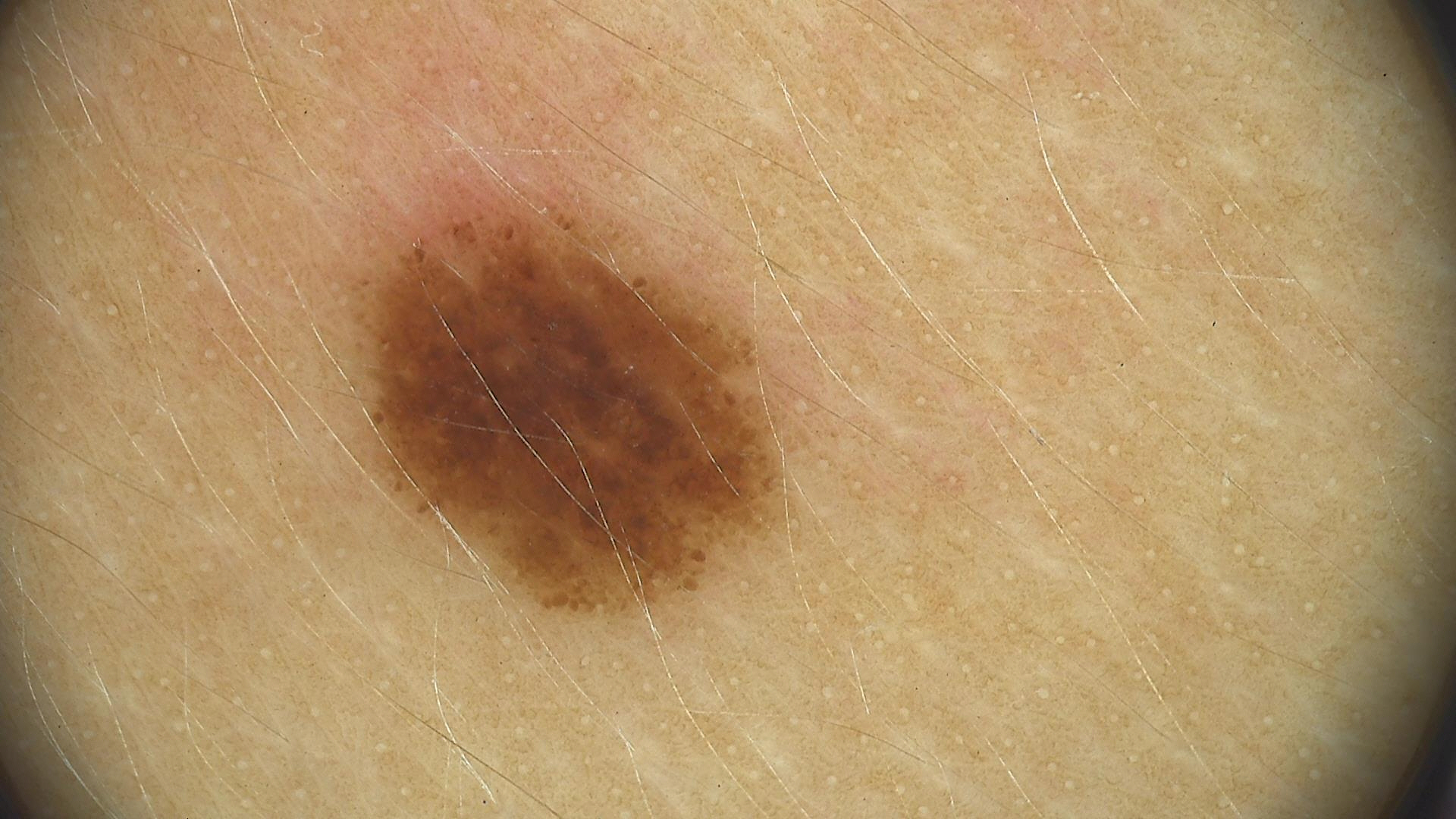A skin lesion imaged with a dermatoscope.
Classified as a dysplastic junctional nevus.